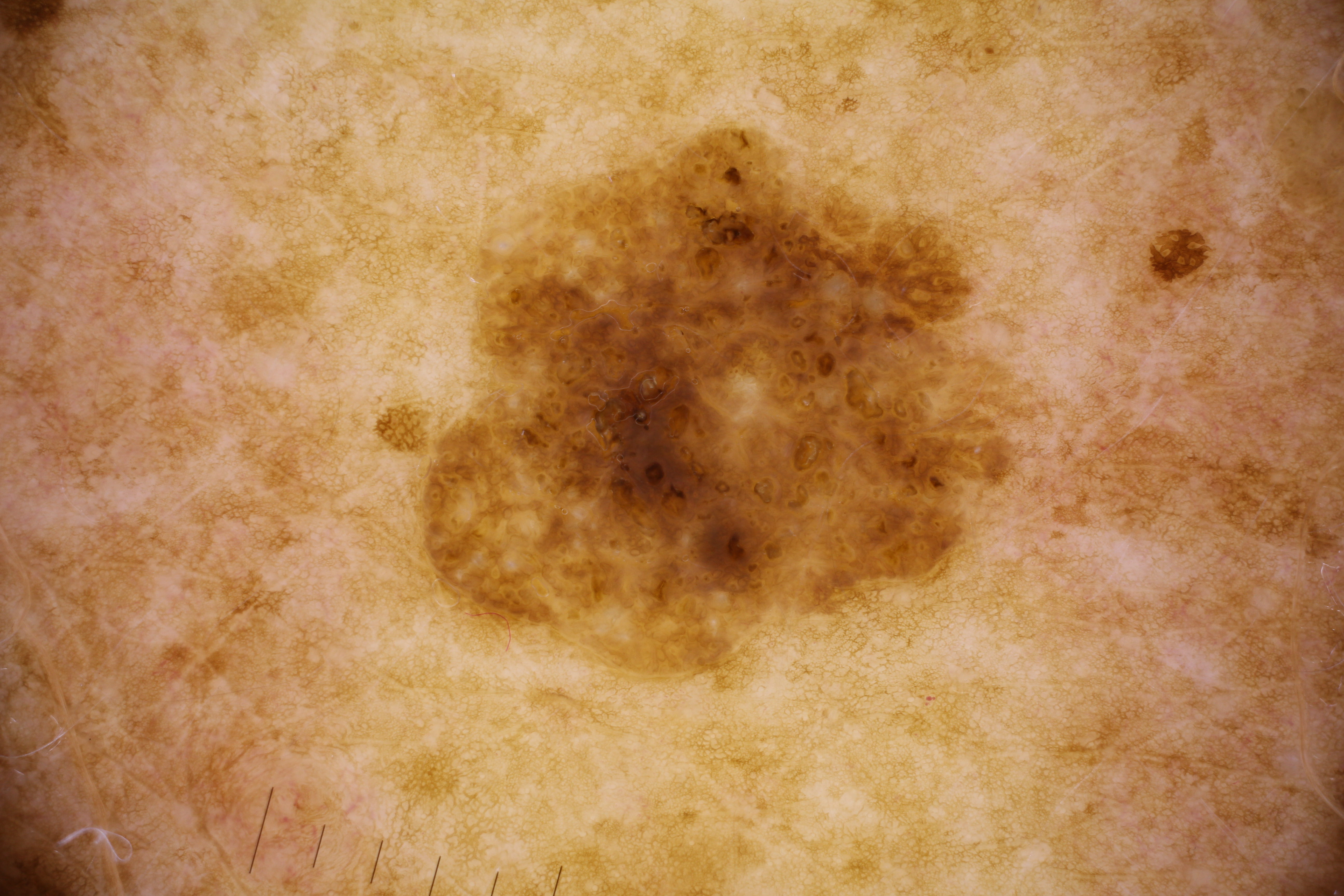A dermoscopy image of a single skin lesion. A female subject approximately 65 years of age. Dermoscopic examination shows pigment network and milia-like cysts. In (x1, y1, x2, y2) order, the lesion is located at bbox(410, 111, 1059, 685). A mid-sized lesion within the field. The diagnostic assessment was a seborrheic keratosis, a benign lesion.